Acquired for a research image collection, with no referral diagnosis — 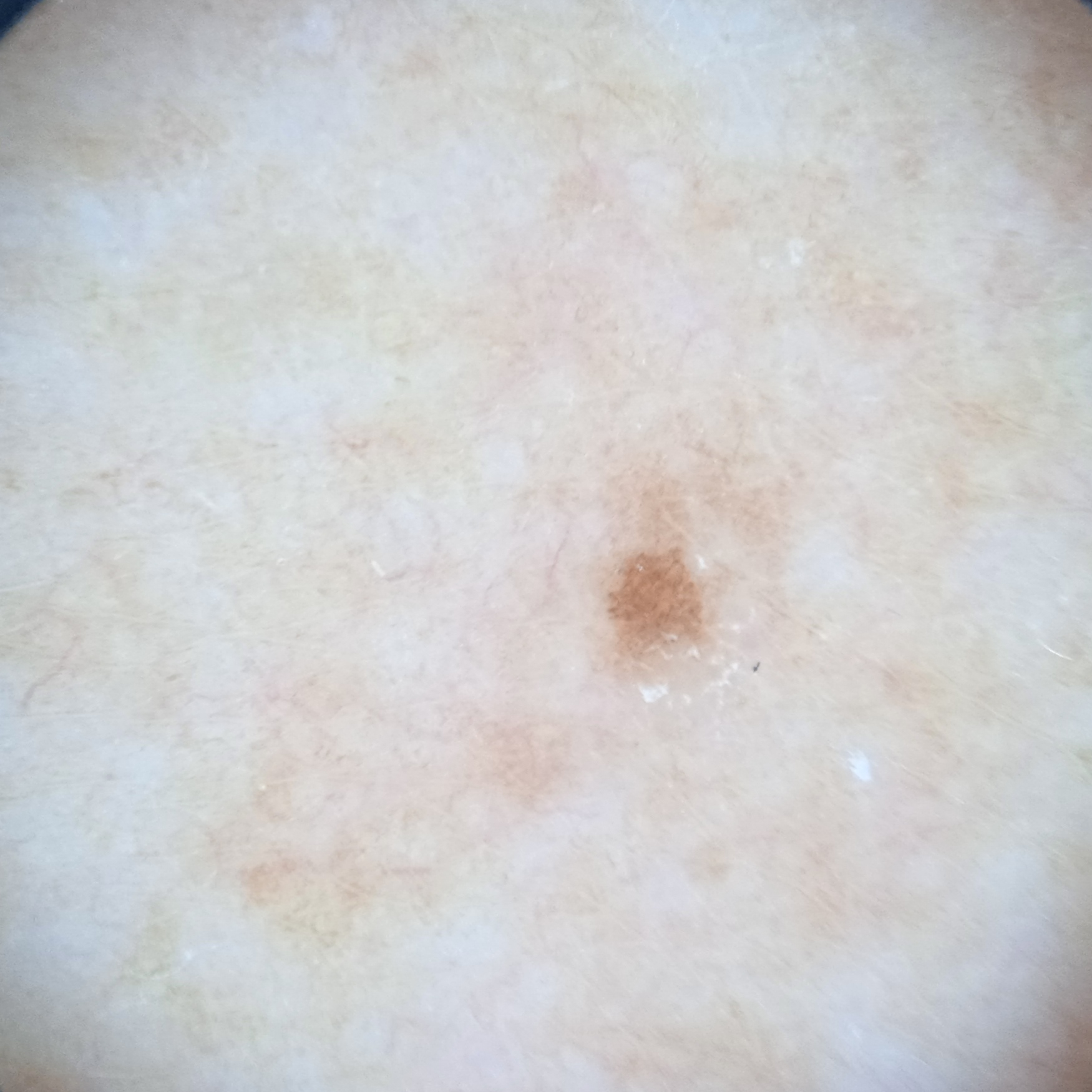The lesion measures approximately 1.3 mm.
The consensus diagnosis for this lesion was a melanocytic nevus.